By history, prior skin cancer (patient or family) and pesticide exposure; a smartphone photograph of a skin lesion; a male patient in their 60s:
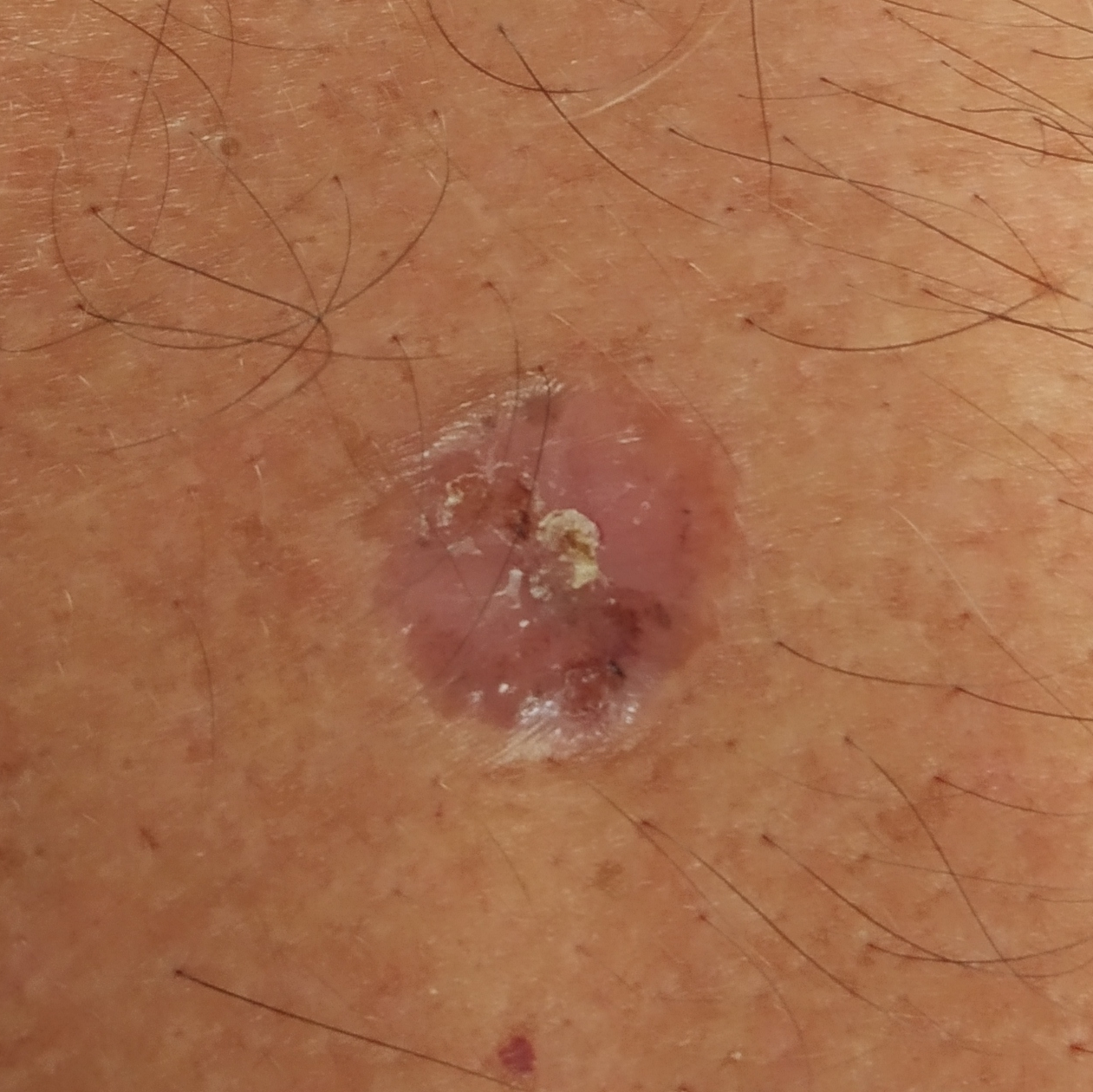• size — 14x13 mm
• symptoms — bleeding, itching, pain, elevation
• pathology — basal cell carcinoma (biopsy-proven)